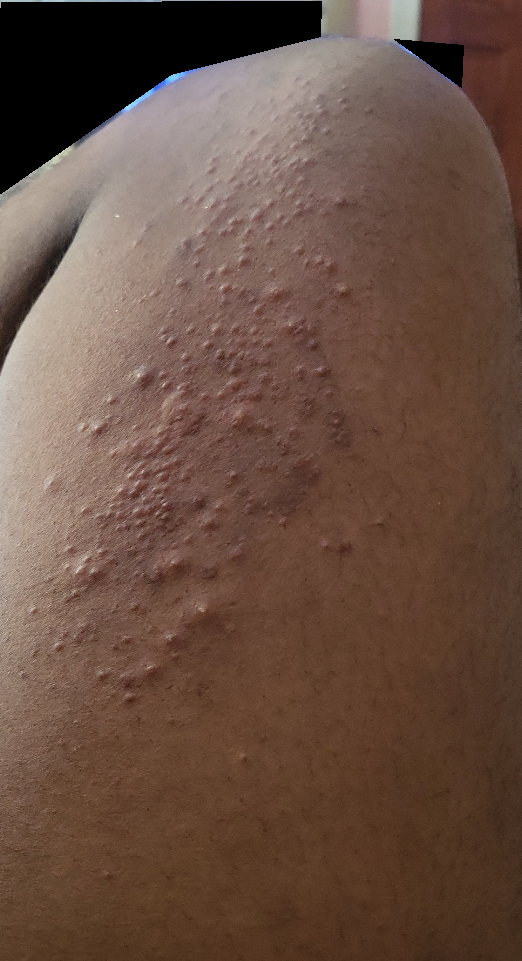{
  "shot_type": "close-up",
  "patient": "male, age 18–29",
  "body_site": "leg",
  "differential": {
    "Urticaria": 0.33,
    "Folliculitis": 0.33,
    "Acute and chronic dermatitis": 0.33
  }
}